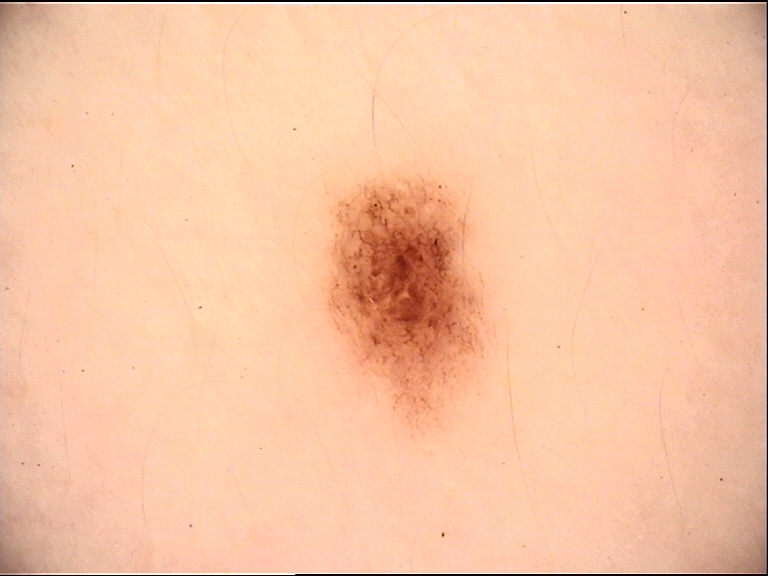A dermoscopic photograph of a skin lesion. Diagnosed as a benign lesion — a dysplastic junctional nevus.